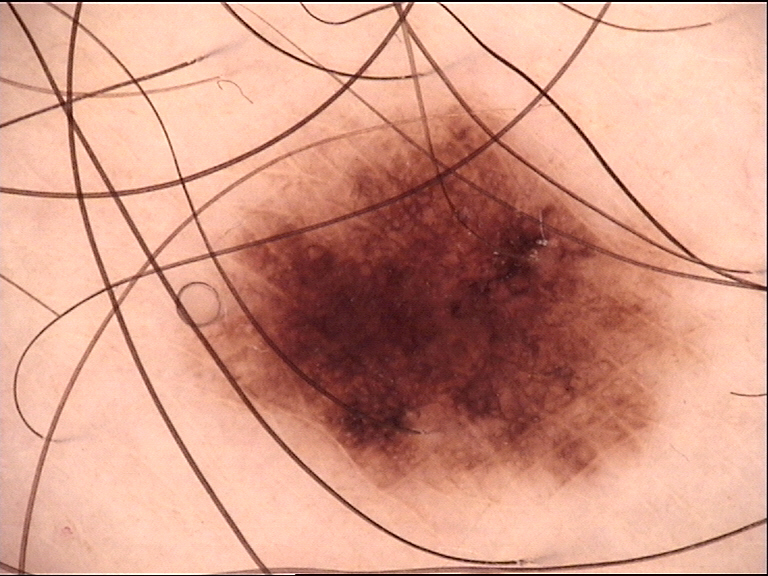Labeled as a dysplastic junctional nevus.